The contributor is 60–69, female. The photo was captured at an angle. The lesion involves the arm:
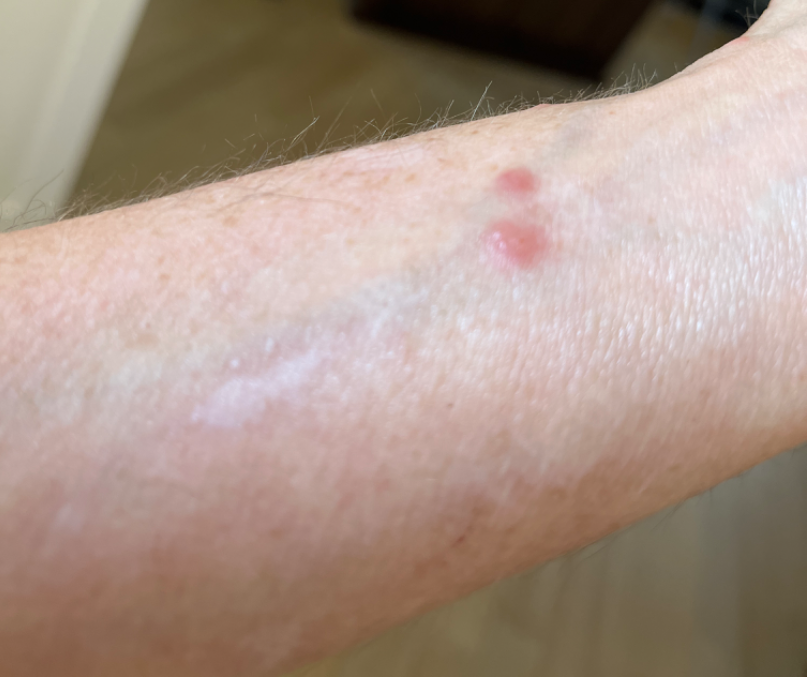The contributor reports itching.
The patient described the issue as a rash.
Reported duration is less than one week.
Most consistent with Insect Bite; less likely is Allergic Contact Dermatitis.